A patient 70 years old; a clinical photo of a skin lesion taken with a smartphone — 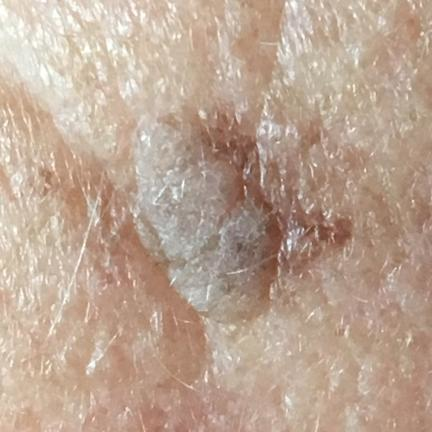Q: Where on the body is the lesion?
A: the face
Q: Any reported symptoms?
A: growth, elevation / no itching
Q: What is this lesion?
A: seborrheic keratosis (clinical consensus)